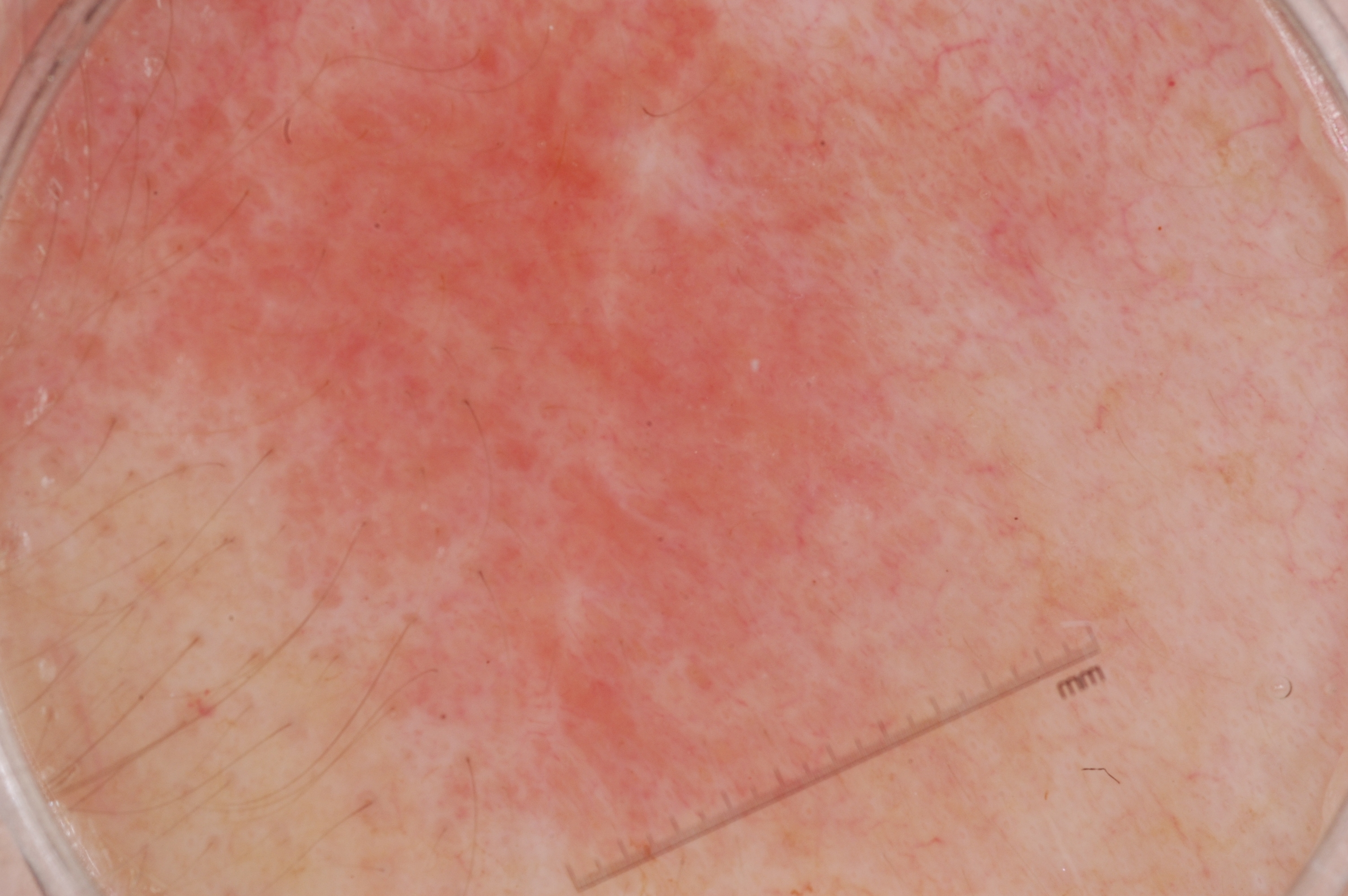Findings:
– image — dermoscopy
– subject — female, aged around 70
– field coverage — spans the dermoscopic field
– absent dermoscopic findings — negative network, streaks, milia-like cysts, and pigment network
– assessment — a melanoma